A wide-field clinical photograph of a skin lesion.
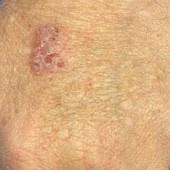The lesion is on an upper extremity.
Confirmed on histopathology as a squamous cell carcinoma.